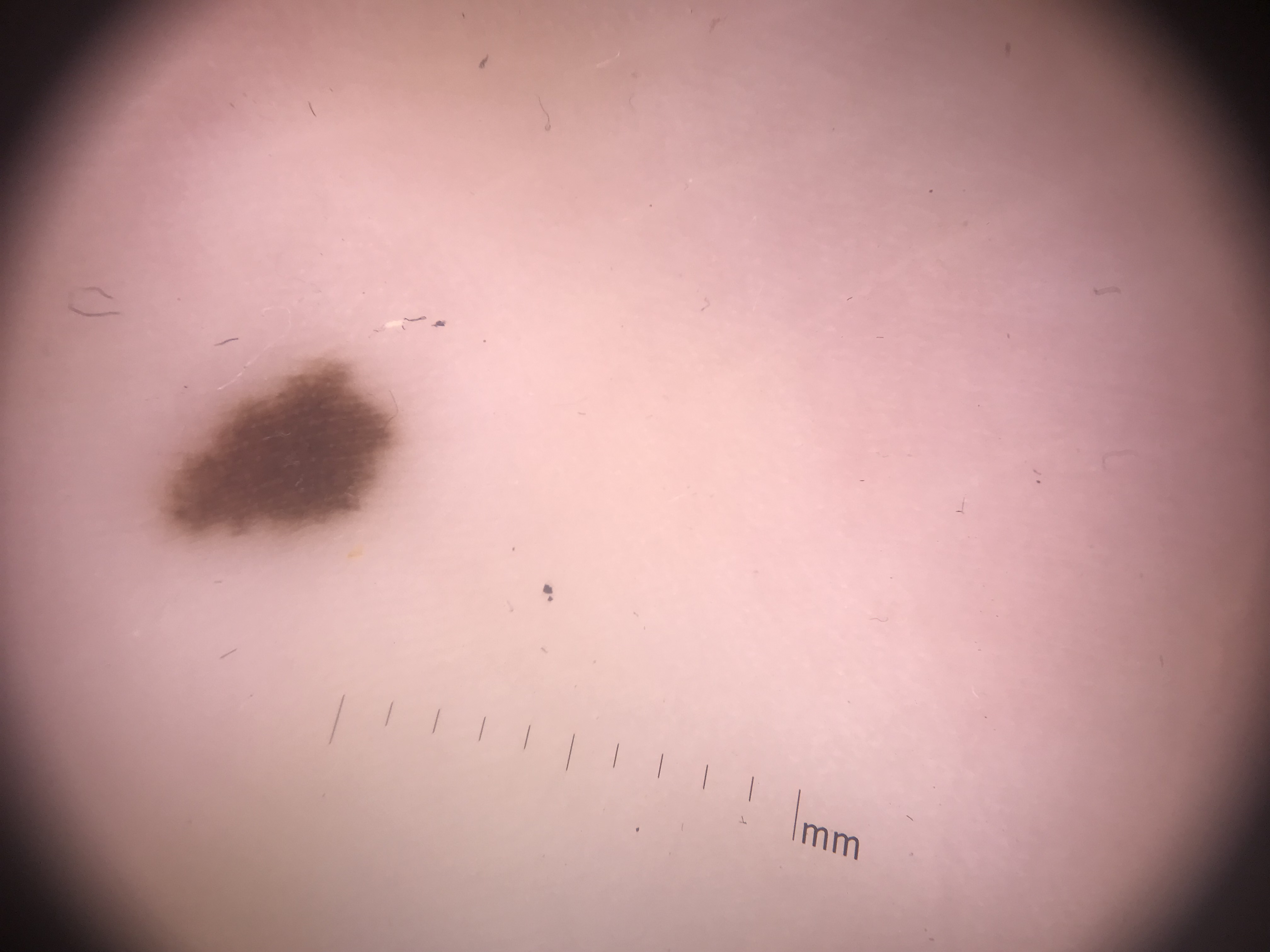modality = dermoscopy; diagnostic label = acral junctional nevus (expert consensus).